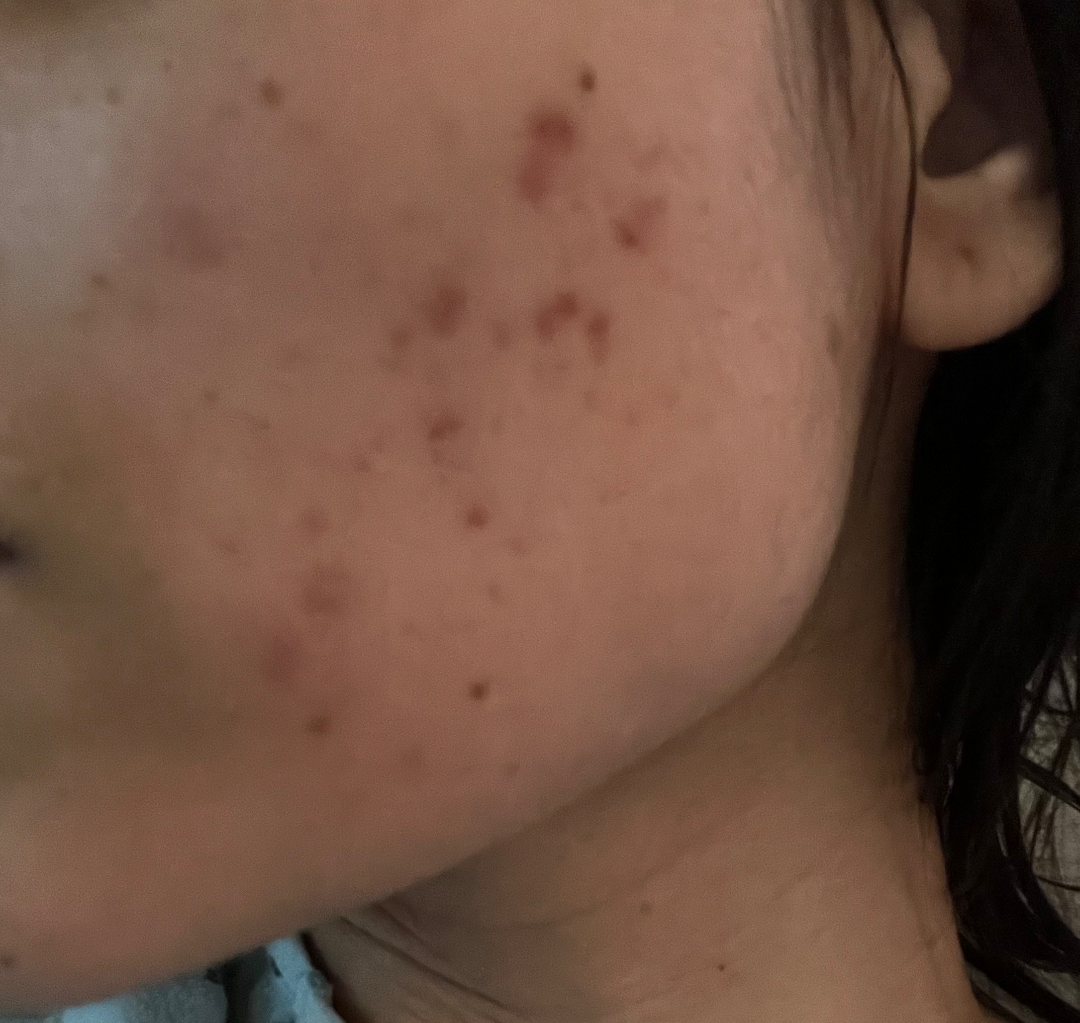present for: one to three months
lesion texture: rough or flaky
subject: female, age 30–39
symptoms: none reported
constitutional symptoms: none reported
shot type: close-up
skin tone: Fitzpatrick IV
diagnostic considerations: the reviewer's impression was Acne